The lesion involves the arm; the photograph is a close-up of the affected area; female contributor, age 18–29:
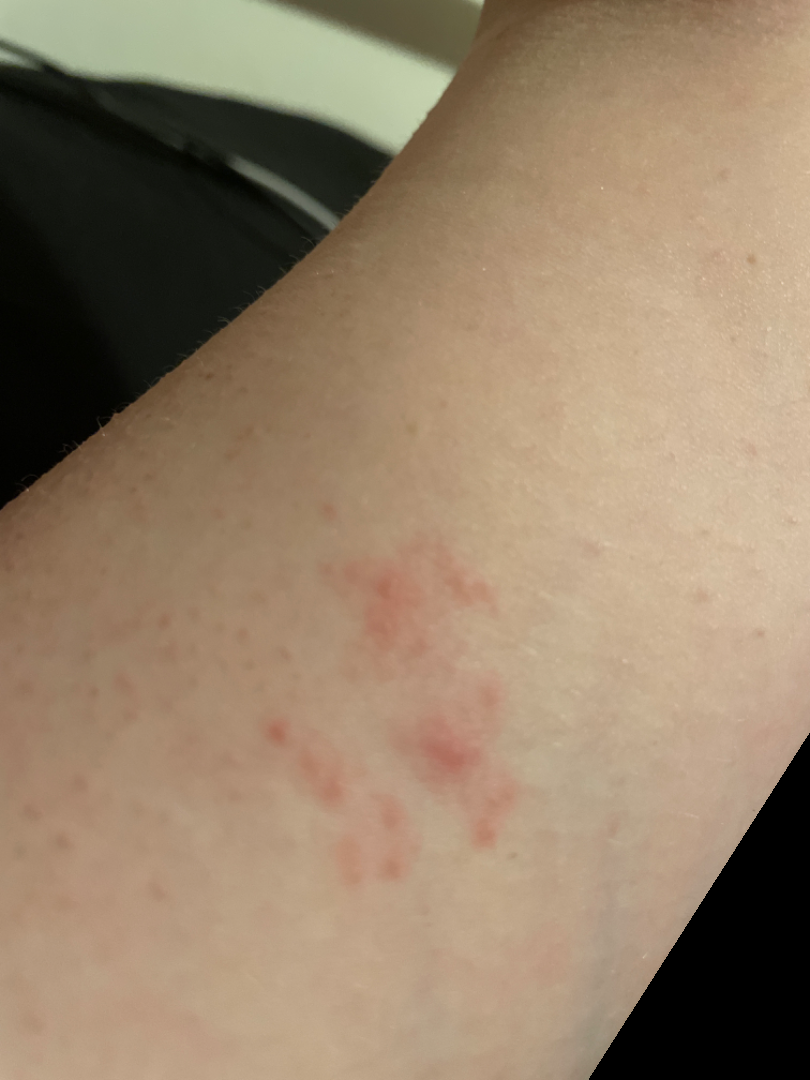Assessment:
Diagnostic features were not clearly distinguishable in this photograph.